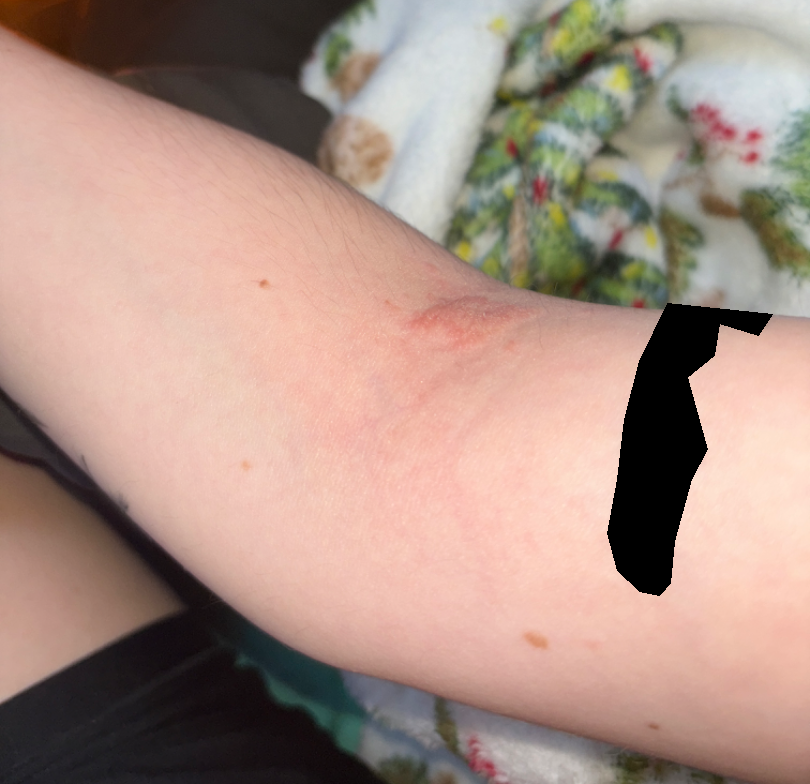Located on the arm. The subject is female. The condition has been present for one to three months. Texture is reported as raised or bumpy and rough or flaky. The patient reported no systemic symptoms. Self-categorized by the patient as a rash. This image was taken at an angle. Symptoms reported: itching and bothersome appearance. Eczema and Allergic Contact Dermatitis were considered with similar weight; a more distant consideration is Infected eczema.